A female subject aged 59 · referred with a clinical suspicion of melanocytic nevus · a macroscopic clinical photograph of a skin lesion.
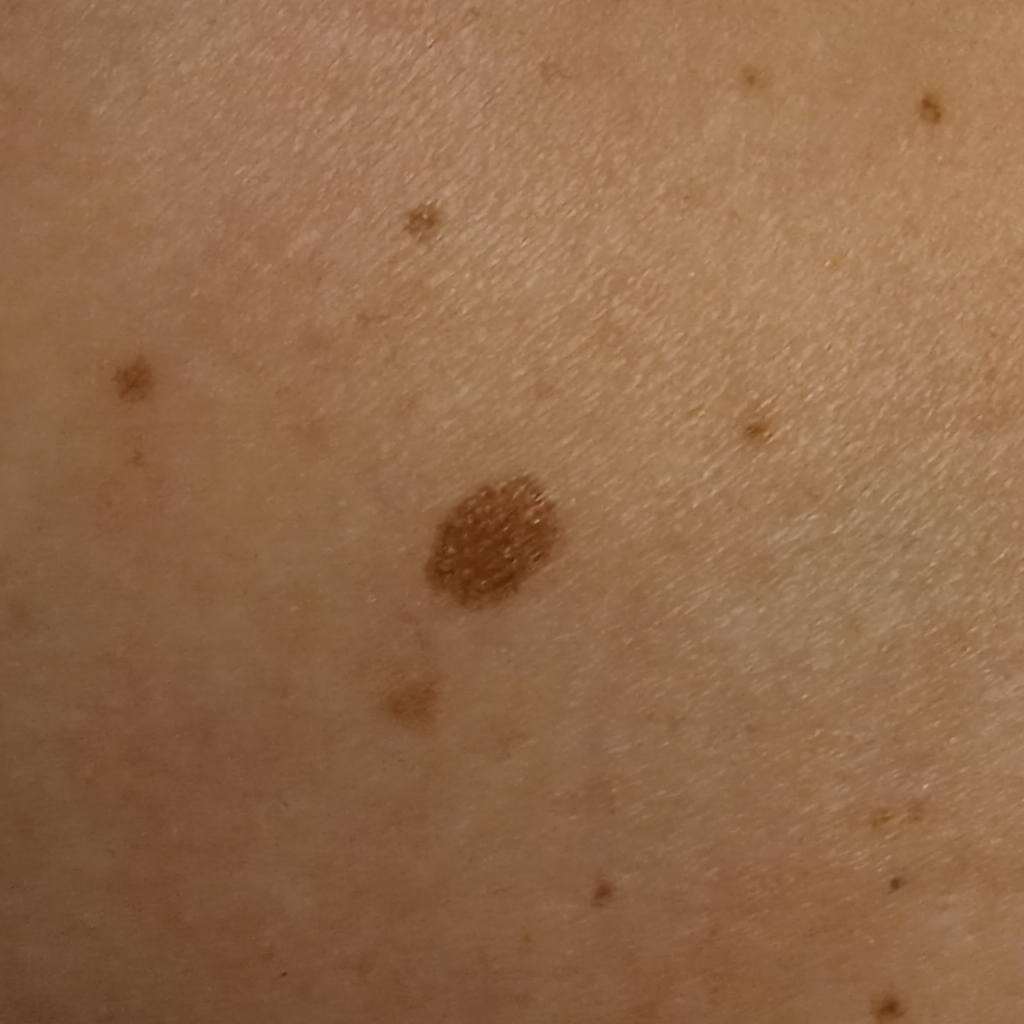Q: What is the anatomic site?
A: an arm
Q: How large is the lesion?
A: 6.7 mm
Q: What did the biopsy show?
A: atypical (dysplastic) nevus — biopsy-proven